Close-up view. No associated lesion symptoms were reported. The lesion is described as flat. The contributor is 30–39, female. The sole of the foot is involved. The patient considered this skin that appeared healthy to them. The condition has been present for less than one week. No constitutional symptoms were reported: 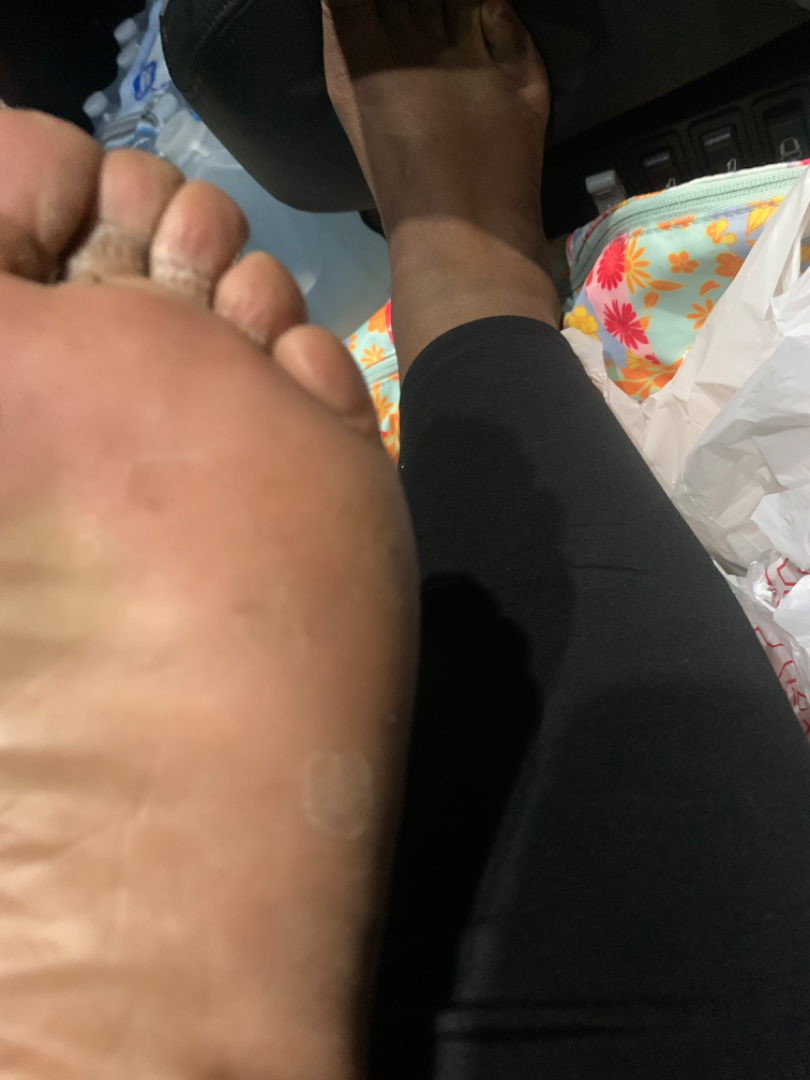assessment=indeterminate.